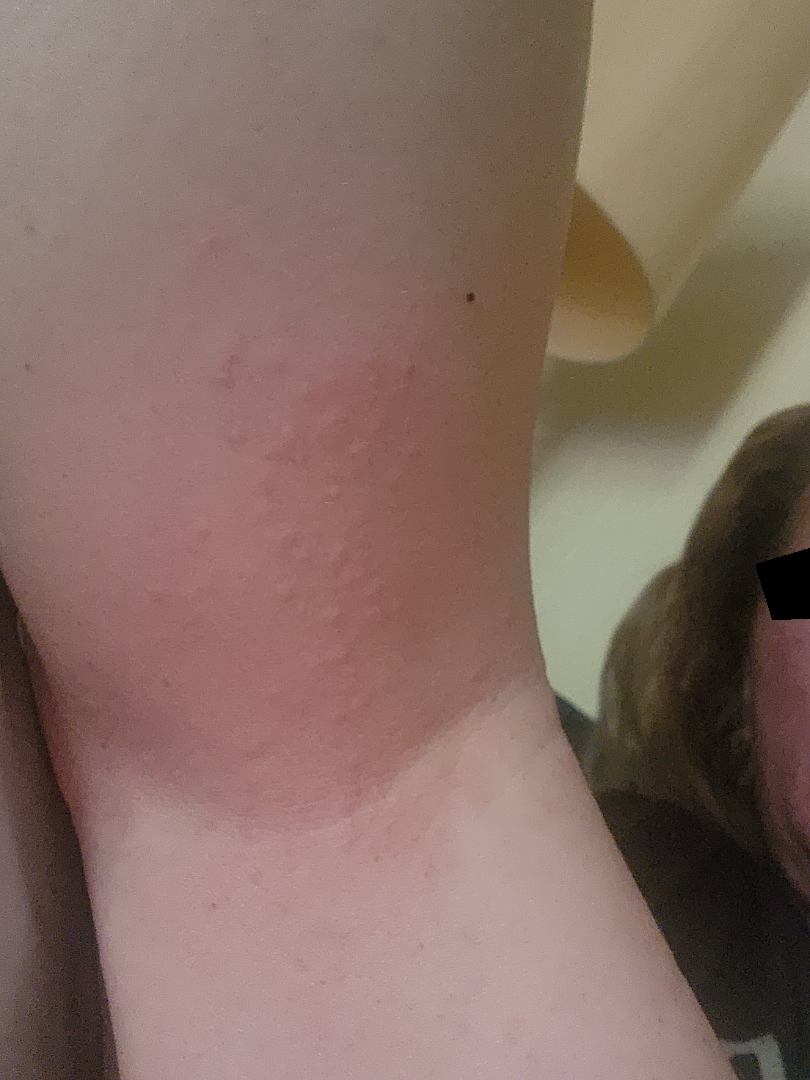The reviewer was unable to grade this case for skin condition. Reported duration is one to four weeks. The leg is involved. The lesion is associated with itching. No associated systemic symptoms reported. Female contributor, age 40–49. Skin tone: Fitzpatrick phototype III. Self-categorized by the patient as a rash. This image was taken at an angle.